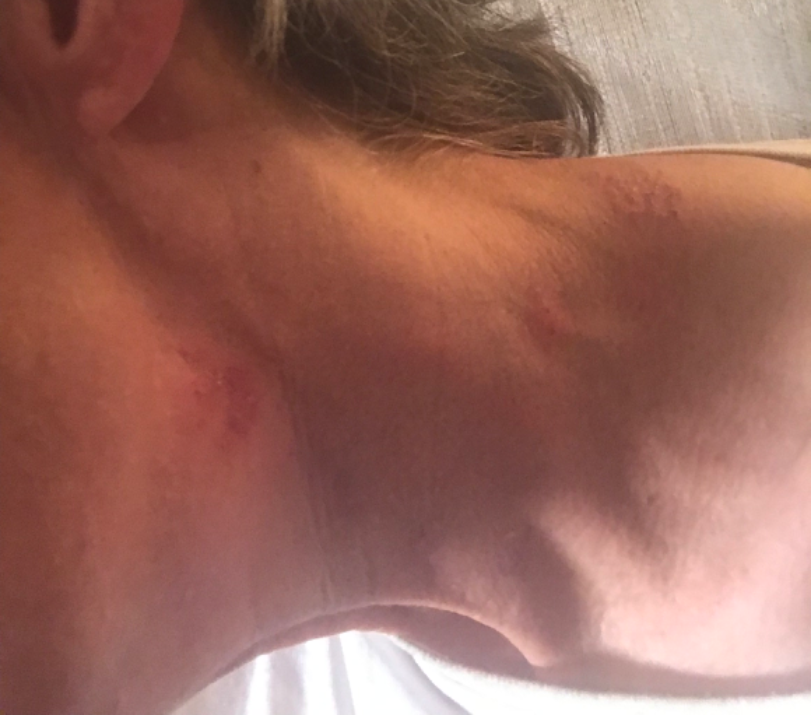Review: The image was not sufficient for the reviewer to characterize the skin condition. Patient information: Non-clinician graders estimated Monk skin tone scale 3 or 4 (two reviewer pools). Reported lesion symptoms include itching and pain. Present for less than one week. This image was taken at a distance. The contributor is a female aged 50–59. The affected area is the head or neck. The patient described the issue as a rash. The patient also reports shortness of breath. The lesion is described as rough or flaky and raised or bumpy.